FST II; non-clinician graders estimated Monk Skin Tone 3–4, the patient indicates itching, the patient indicates the condition has been present for about one day, the patient considered this a rash, located on the arm, an image taken at a distance, texture is reported as raised or bumpy:
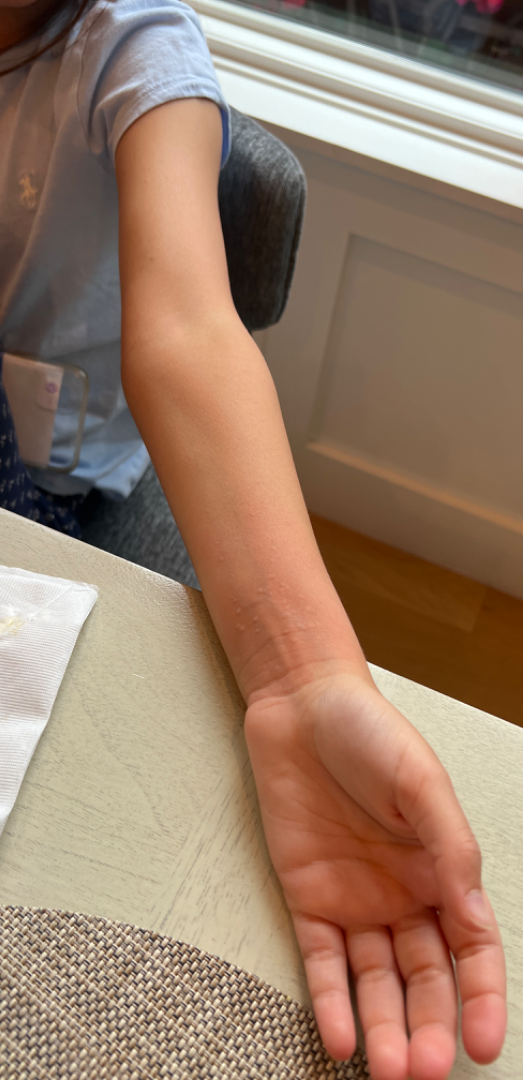{"differential": {"leading": ["Urticaria"], "considered": ["Verruca vulgaris", "Allergic Contact Dermatitis"]}}